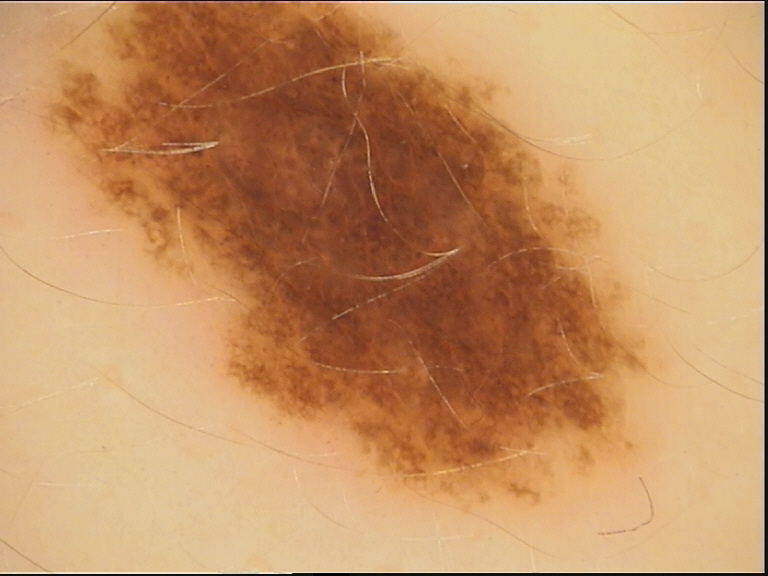diagnosis — dysplastic junctional nevus (expert consensus)